A skin lesion imaged with contact-polarized dermoscopy — 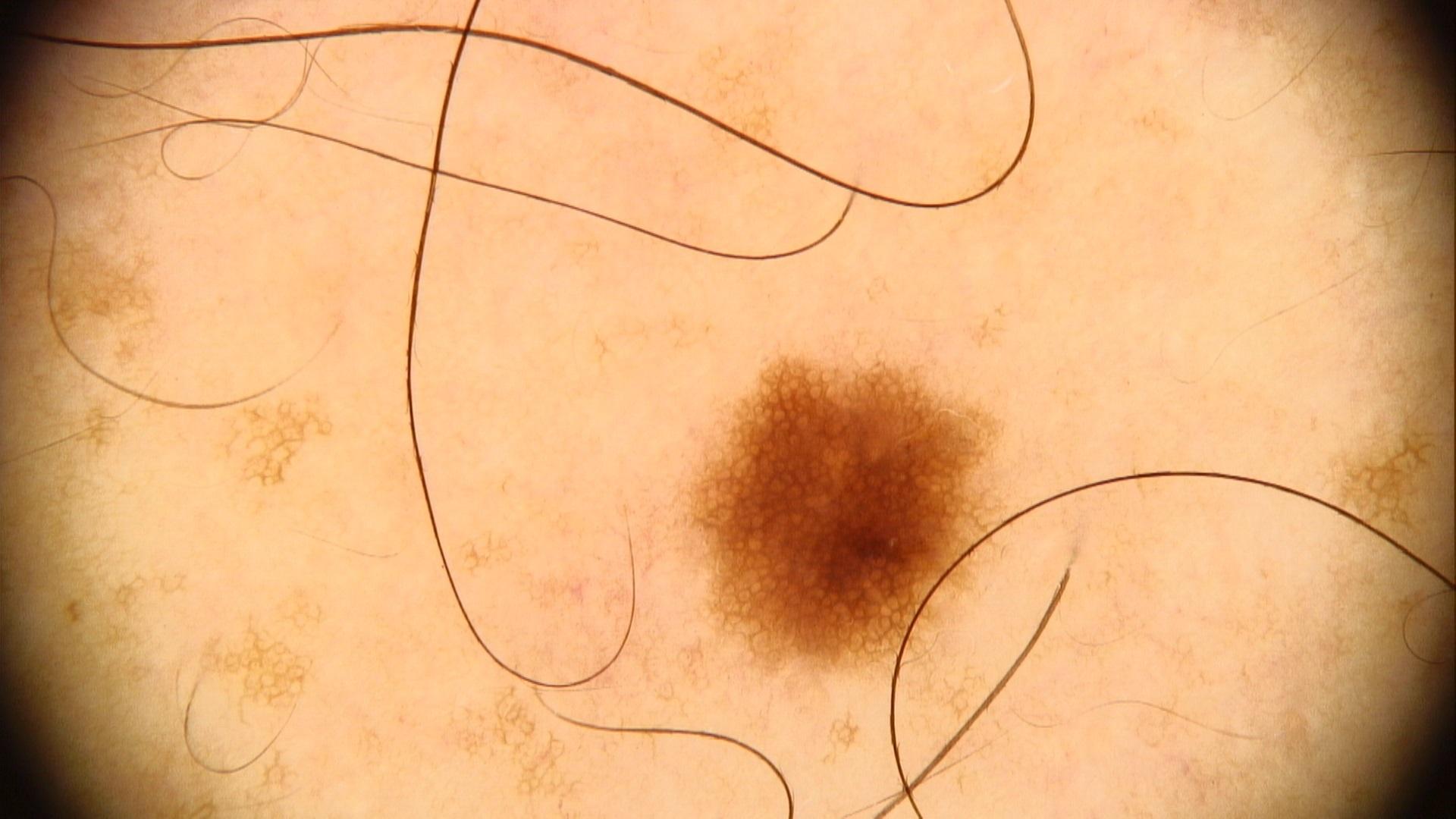Q: What is the anatomic site?
A: the trunk
Q: What is this lesion?
A: Nevus